This image was taken at a distance; the affected area is the arm.
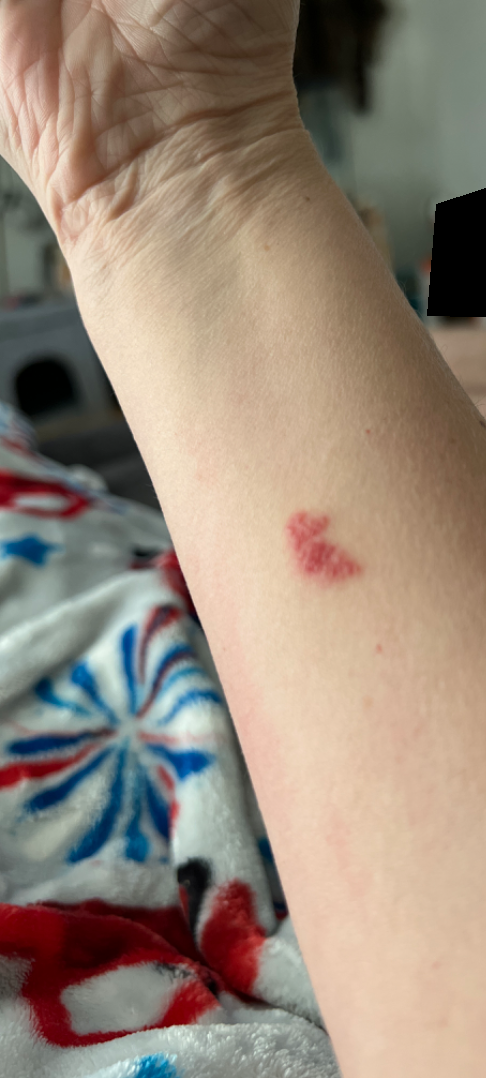<dermatology_case>
  <assessment>not assessable</assessment>
  <texture>fluid-filled, raised or bumpy</texture>
</dermatology_case>